The patient says their skin reddens with sun exposure. The referring clinician suspected melanocytic nevus. Few moles overall by the patient's own estimate. A female subject age 15. A macroscopic clinical photograph of a skin lesion: 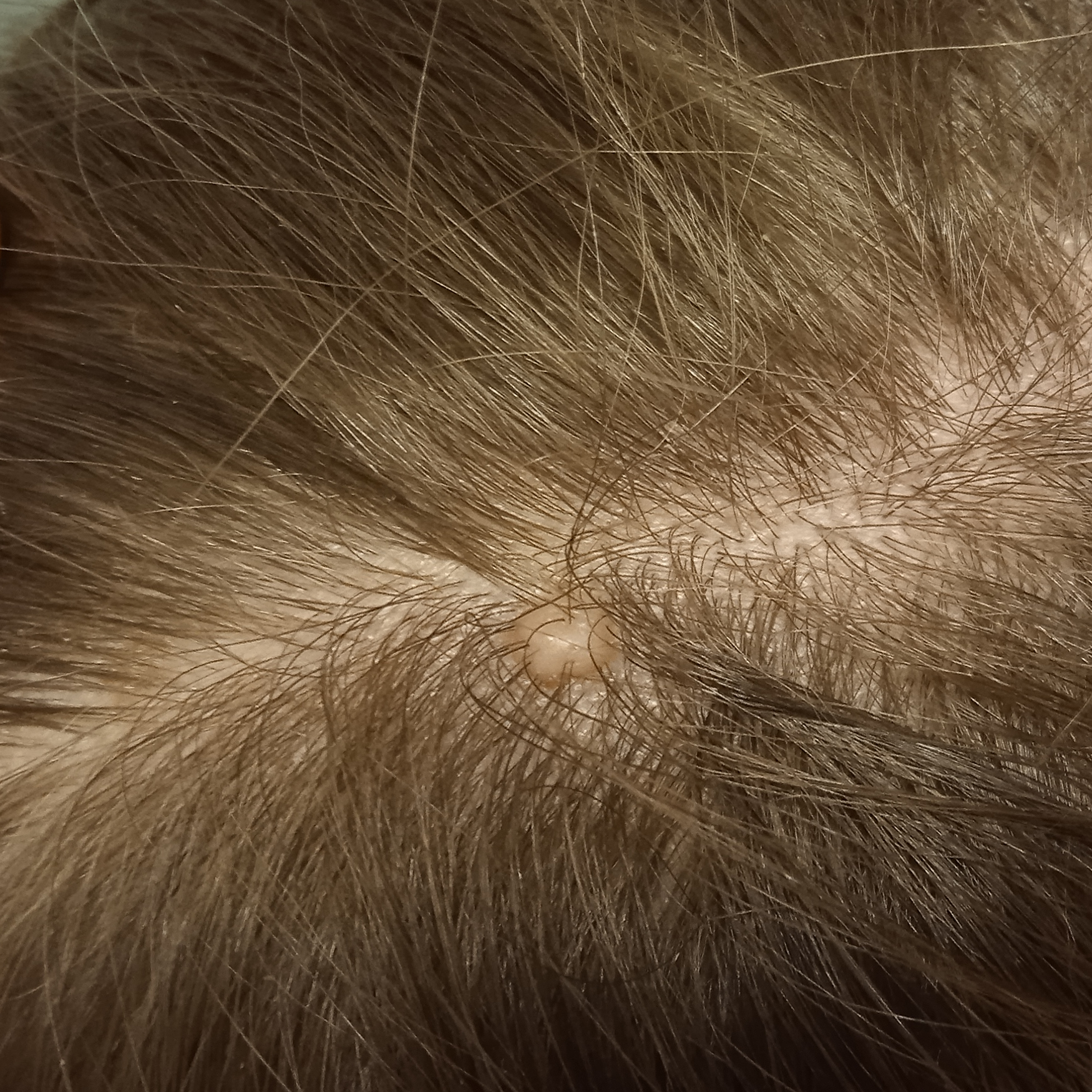| field | value |
|---|---|
| body site | the head |
| size | 5 mm |
| pathology | melanocytic nevus (biopsy-proven) |